The photograph is a close-up of the affected area; the affected area is the head or neck, leg and arm — 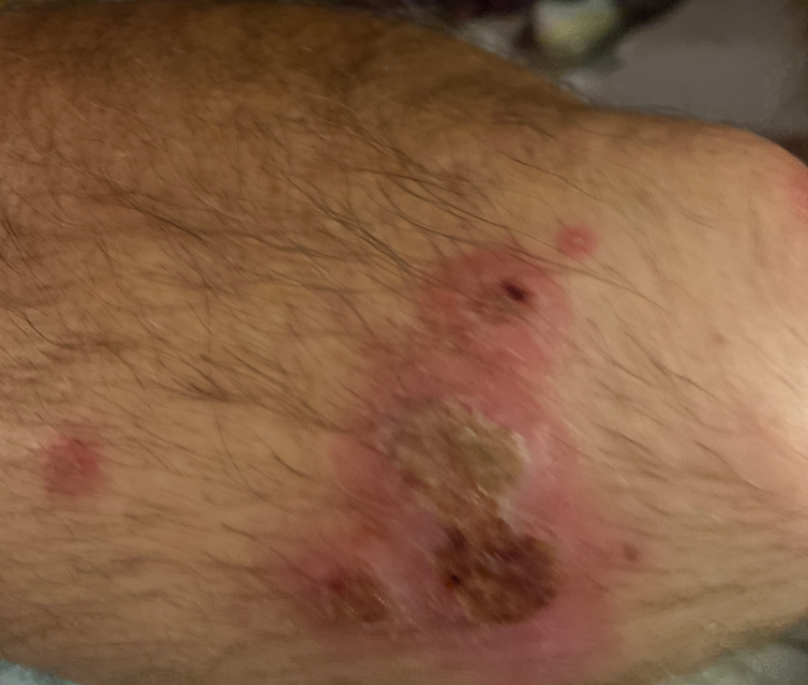Q: What was the assessment?
A: unable to determine